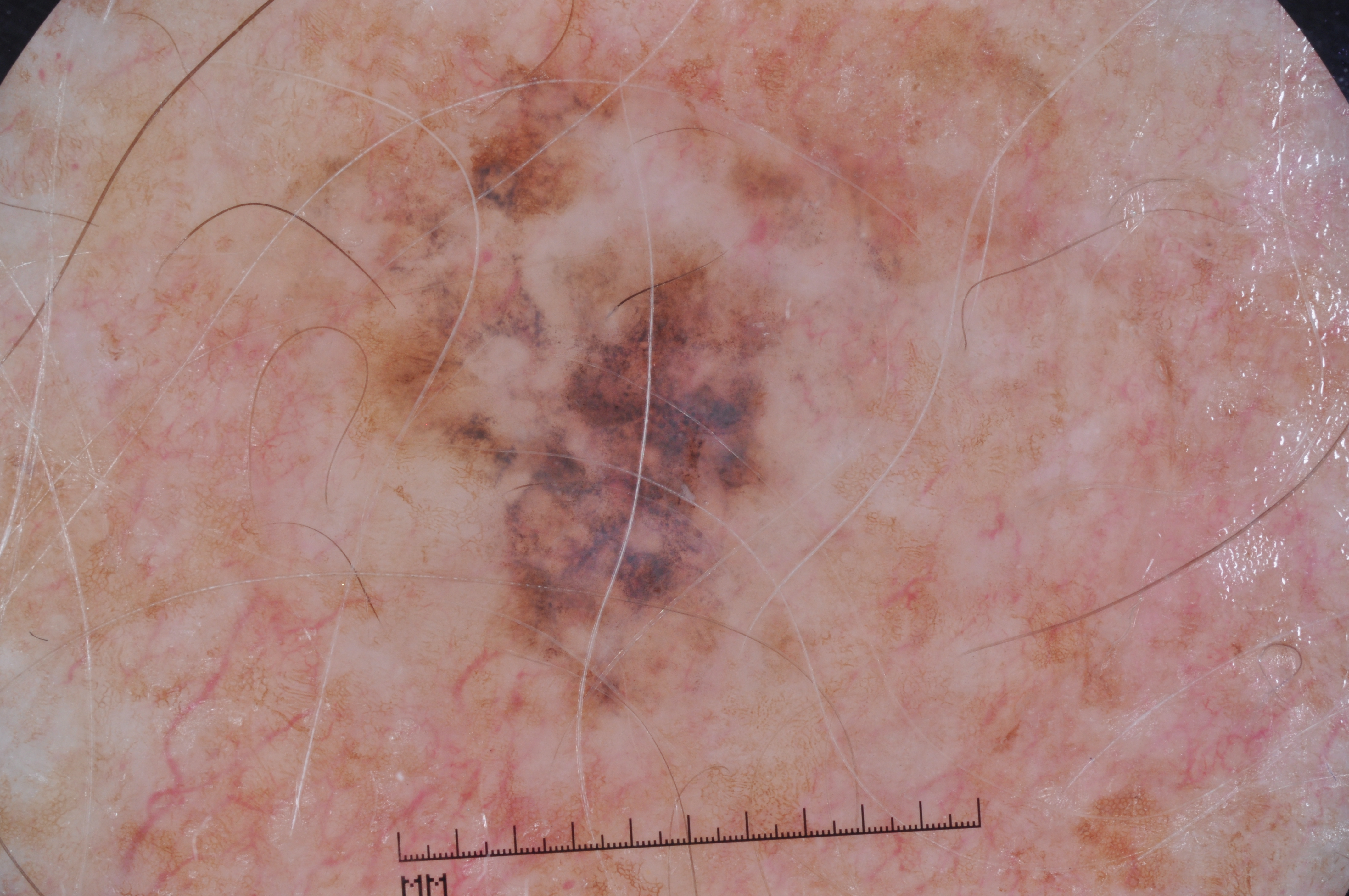patient = male, in their mid- to late 70s
imaging = dermoscopic image
dermoscopic pattern = pigment network
location = bbox=[291, 27, 967, 749]
diagnostic label = a melanoma